The patient is FST II. A clinical close-up photograph of a skin lesion. A male patient 80 years of age: 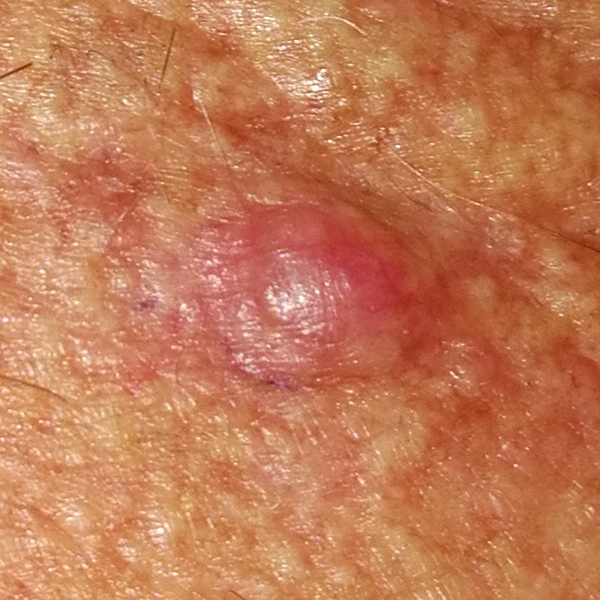The lesion is located on the neck.
The lesion is roughly 5 by 5 mm.
Per patient report, the lesion has grown, is elevated, and itches.
Histopathological examination showed a malignant lesion — a basal cell carcinoma.